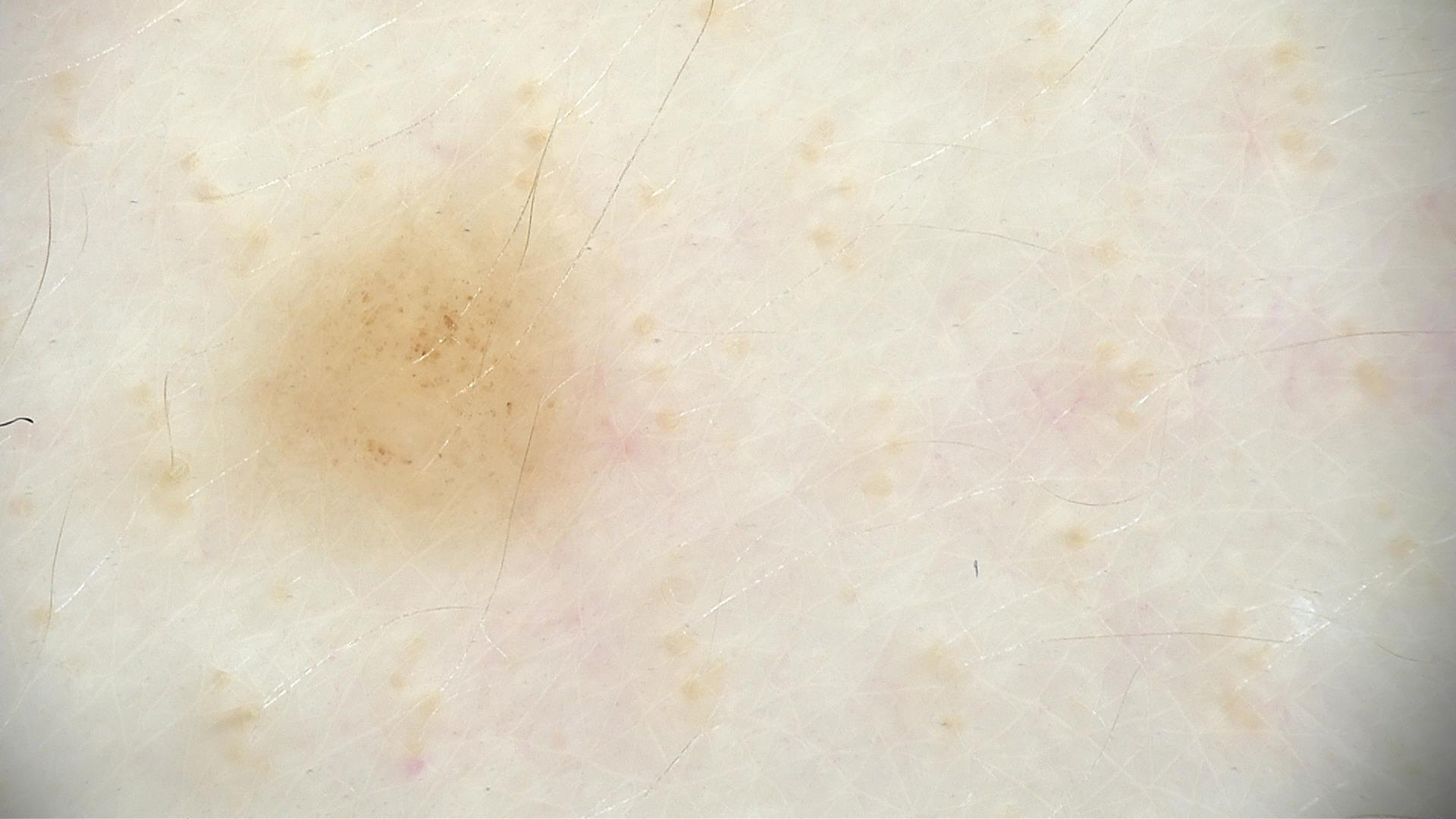Conclusion:
Consistent with a dysplastic junctional nevus.